A dermoscopic view of a skin lesion.
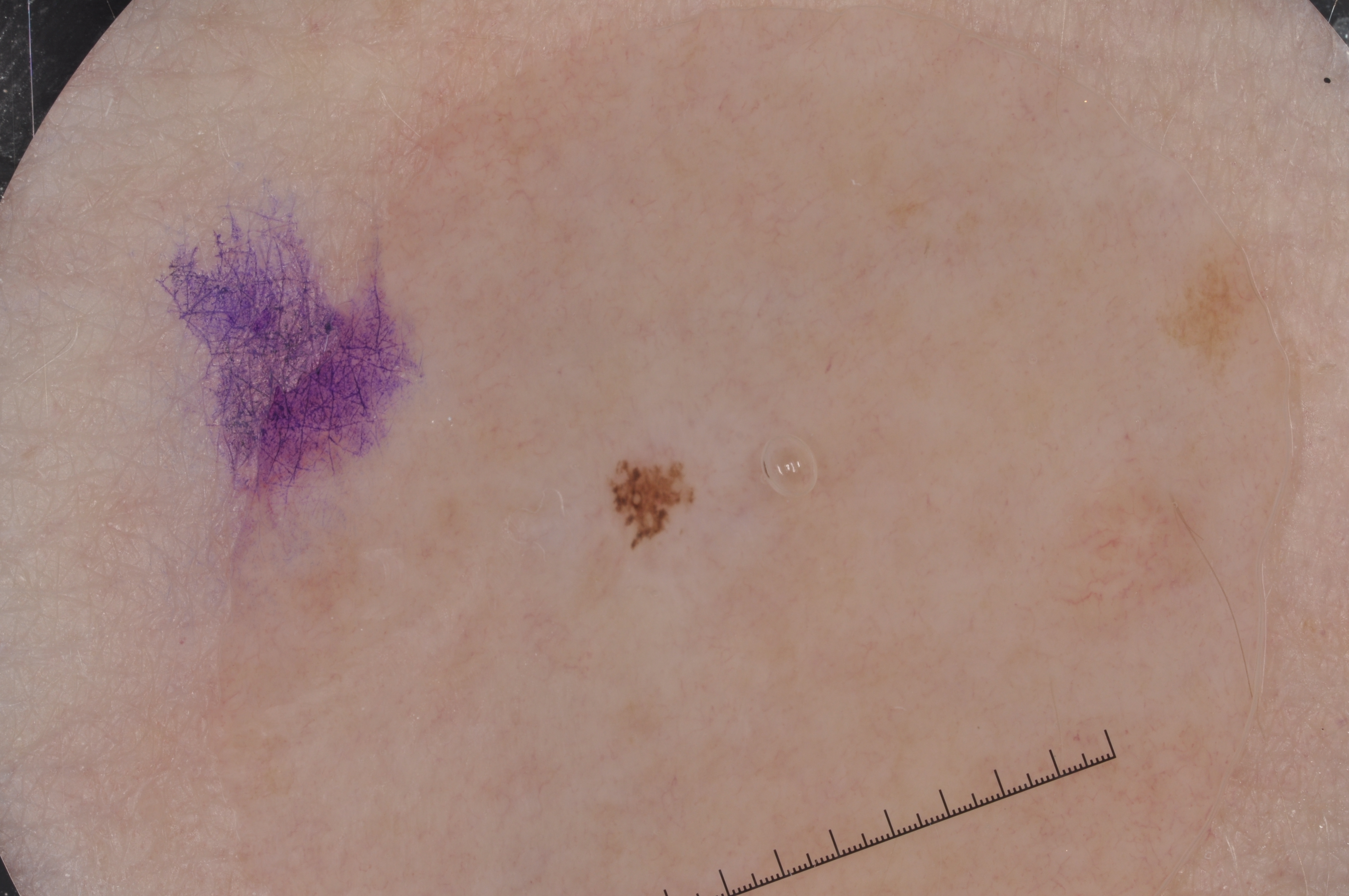Findings: With coordinates (x1, y1, x2, y2), the lesion occupies the region 605 457 695 551. Impression: The clinical diagnosis was a melanocytic nevus.